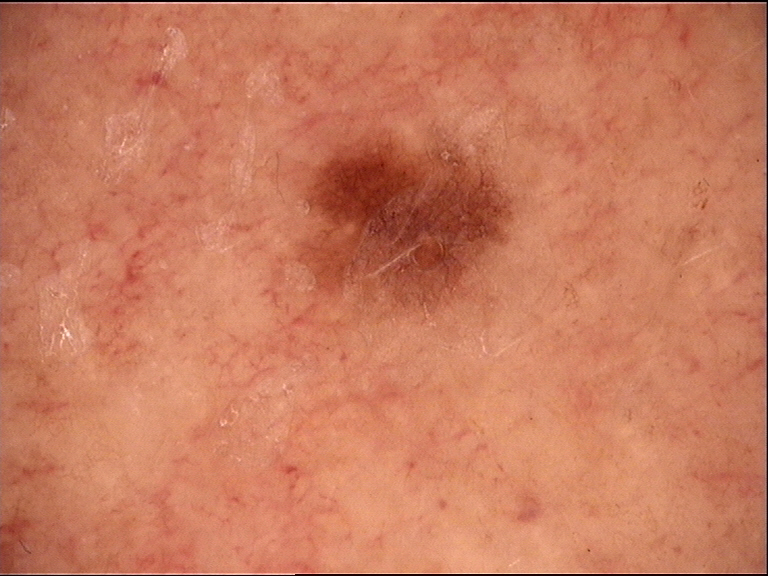diagnostic label: dysplastic junctional nevus (expert consensus)